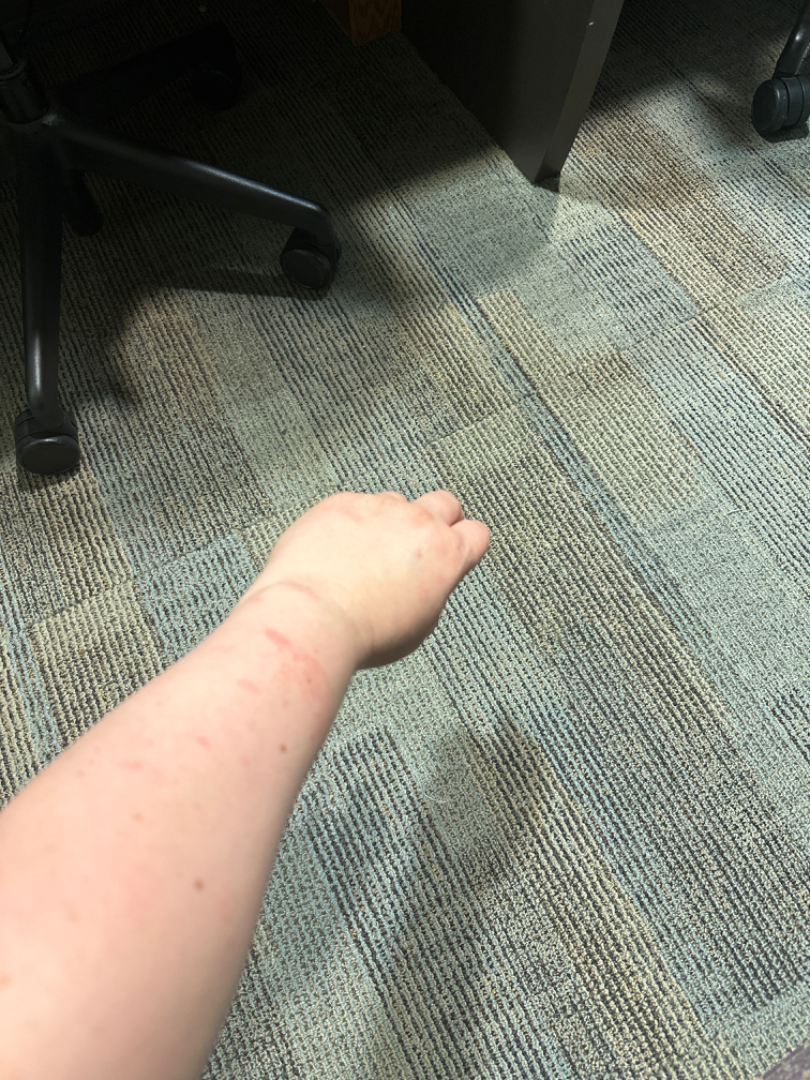photo taken = at a distance | present for = three to twelve months | subject = female | anatomic site = arm and leg | patient's own categorization = skin that appeared healthy to them | differential diagnosis = reviewed remotely by three dermatologists: most likely Eczema; also consider Allergic Contact Dermatitis; with consideration of Acute dermatitis, NOS.